The photo was captured at an angle:
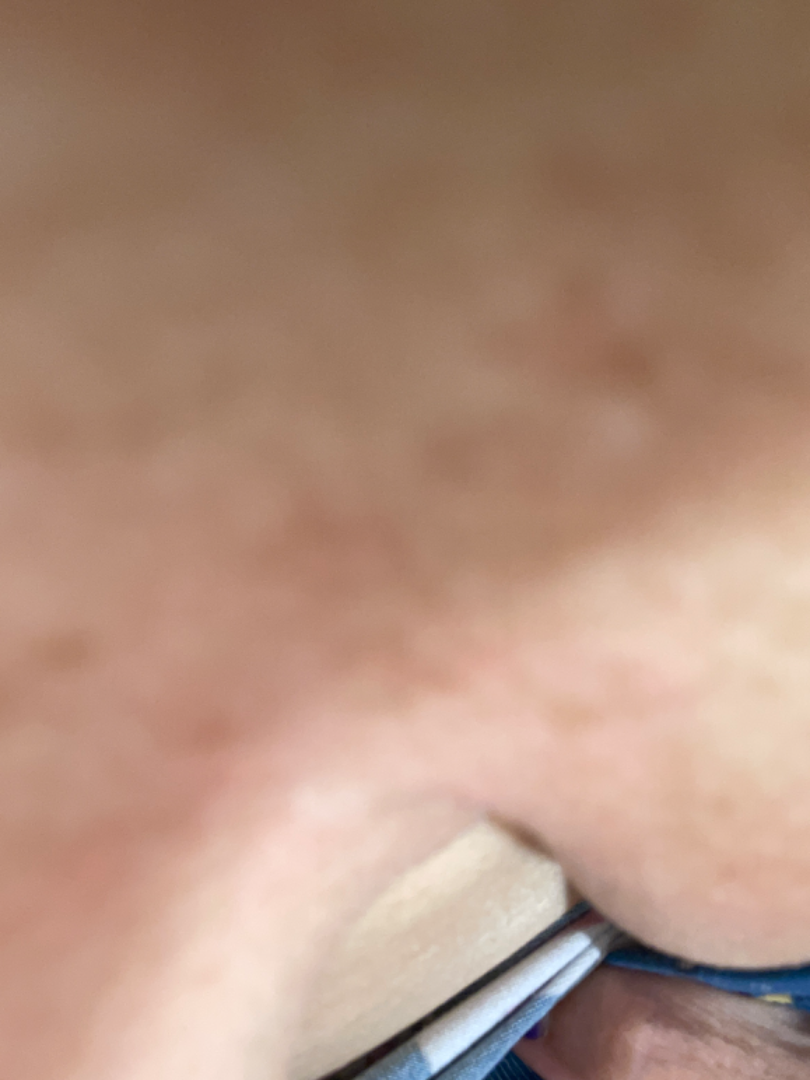The case was indeterminate on photographic review.